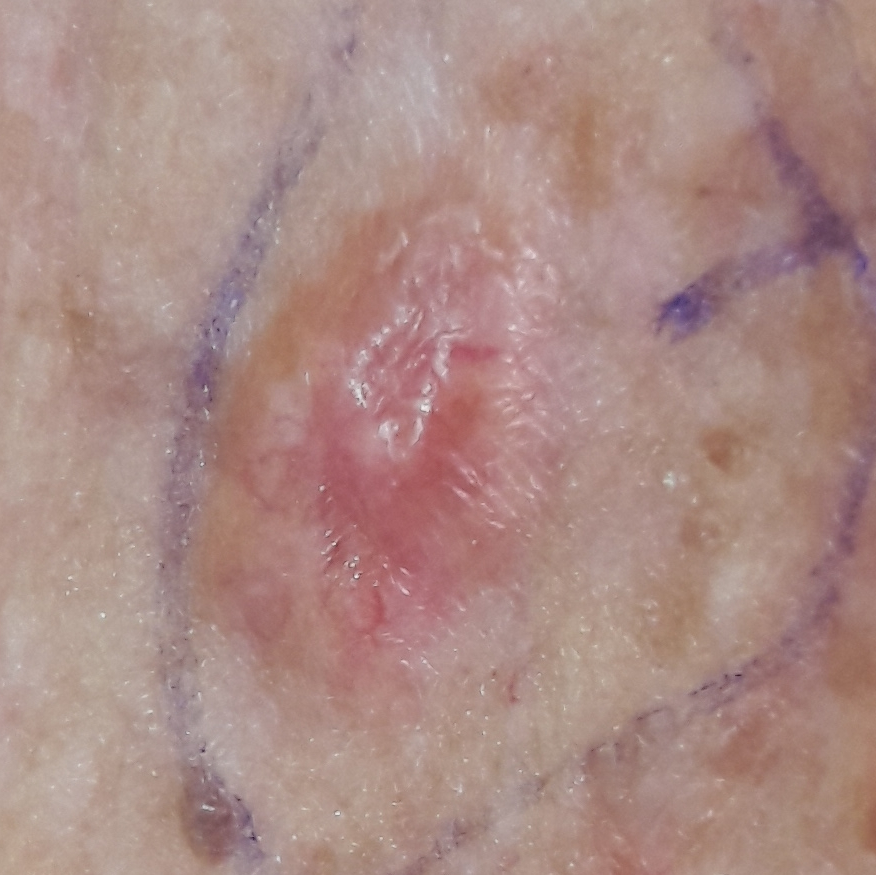imaging = clinical photograph | patient = female, 57 years of age | region = the chest | symptoms = elevation, bleeding | diagnosis = basal cell carcinoma (biopsy-proven).